A male subject, in their 30s; a dermoscopic image of a skin lesion:
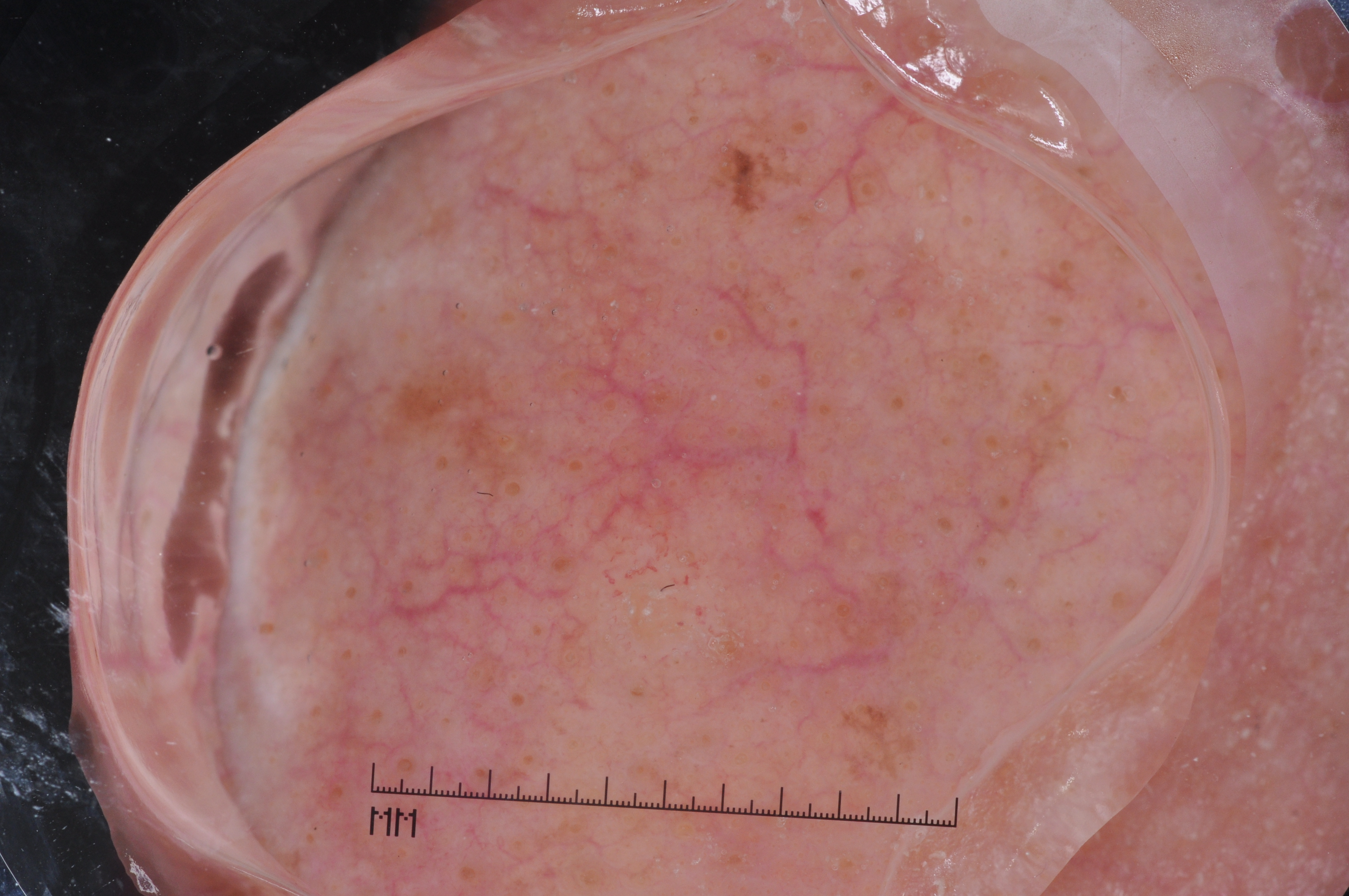Image and clinical context:
The lesion's extent is 235 35 1129 863. Dermoscopy demonstrates no milia-like cysts, streaks, pigment network, or negative network. The lesion occupies roughly 47% of the field.
Assessment:
Diagnosed as a seborrheic keratosis, a benign lesion.